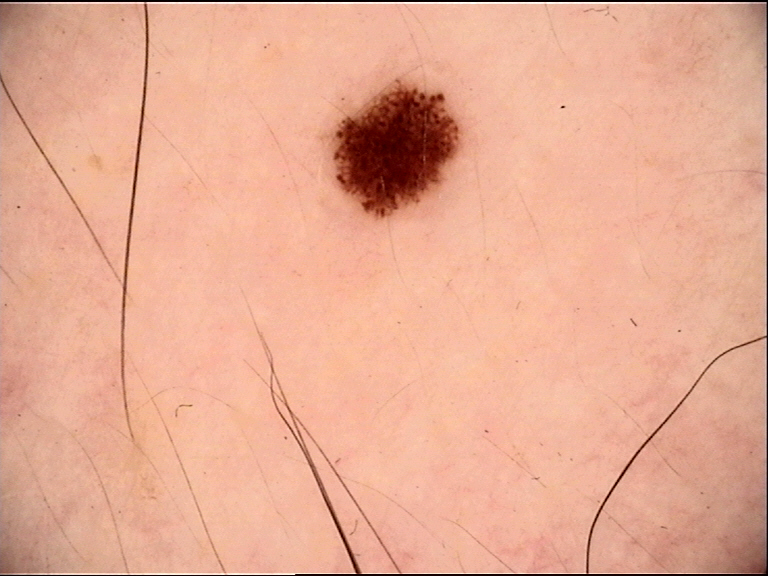Consistent with a dysplastic junctional nevus.